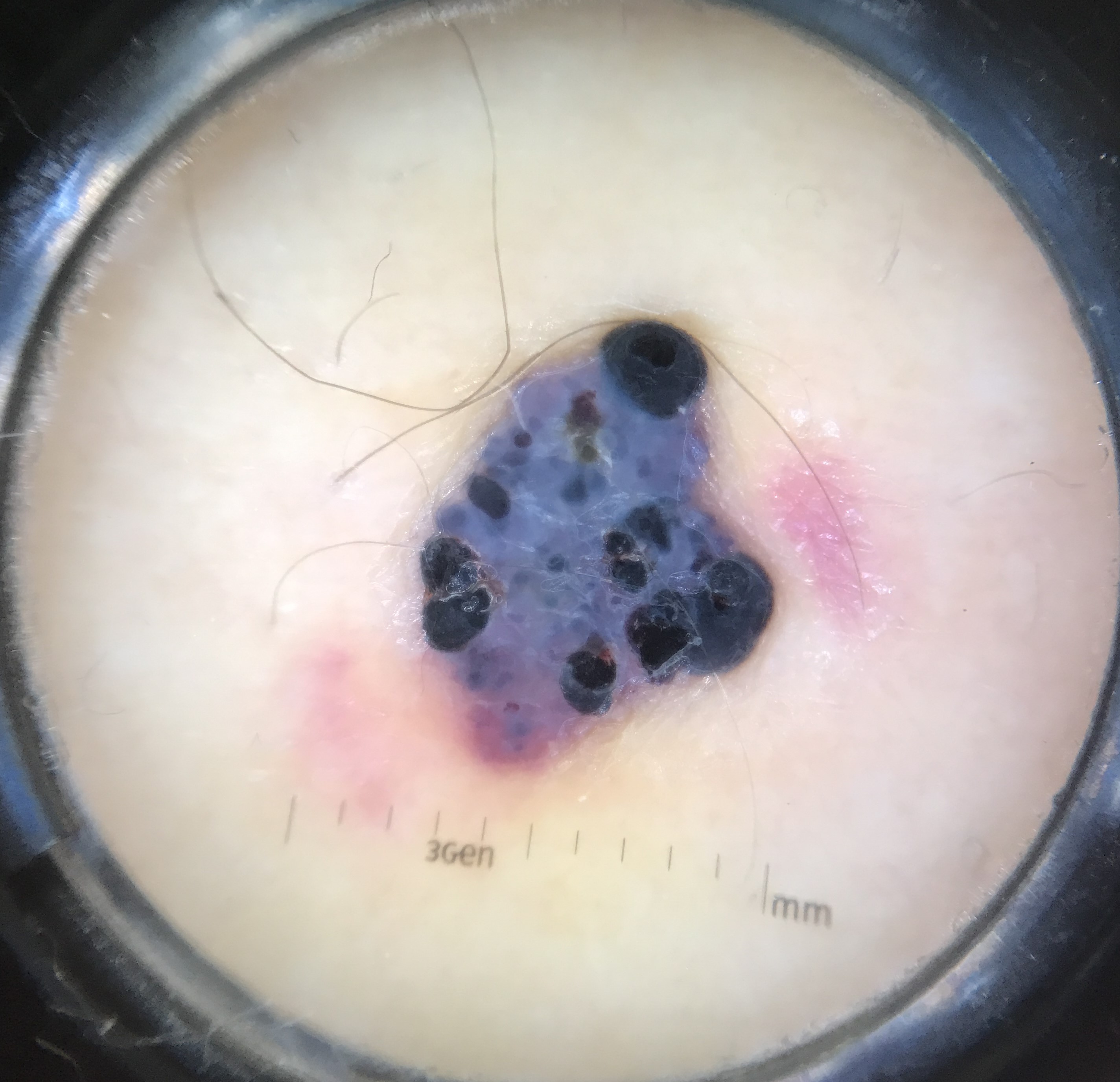Conclusion: The diagnosis was an angiokeratoma.